A skin lesion imaged with a dermatoscope.
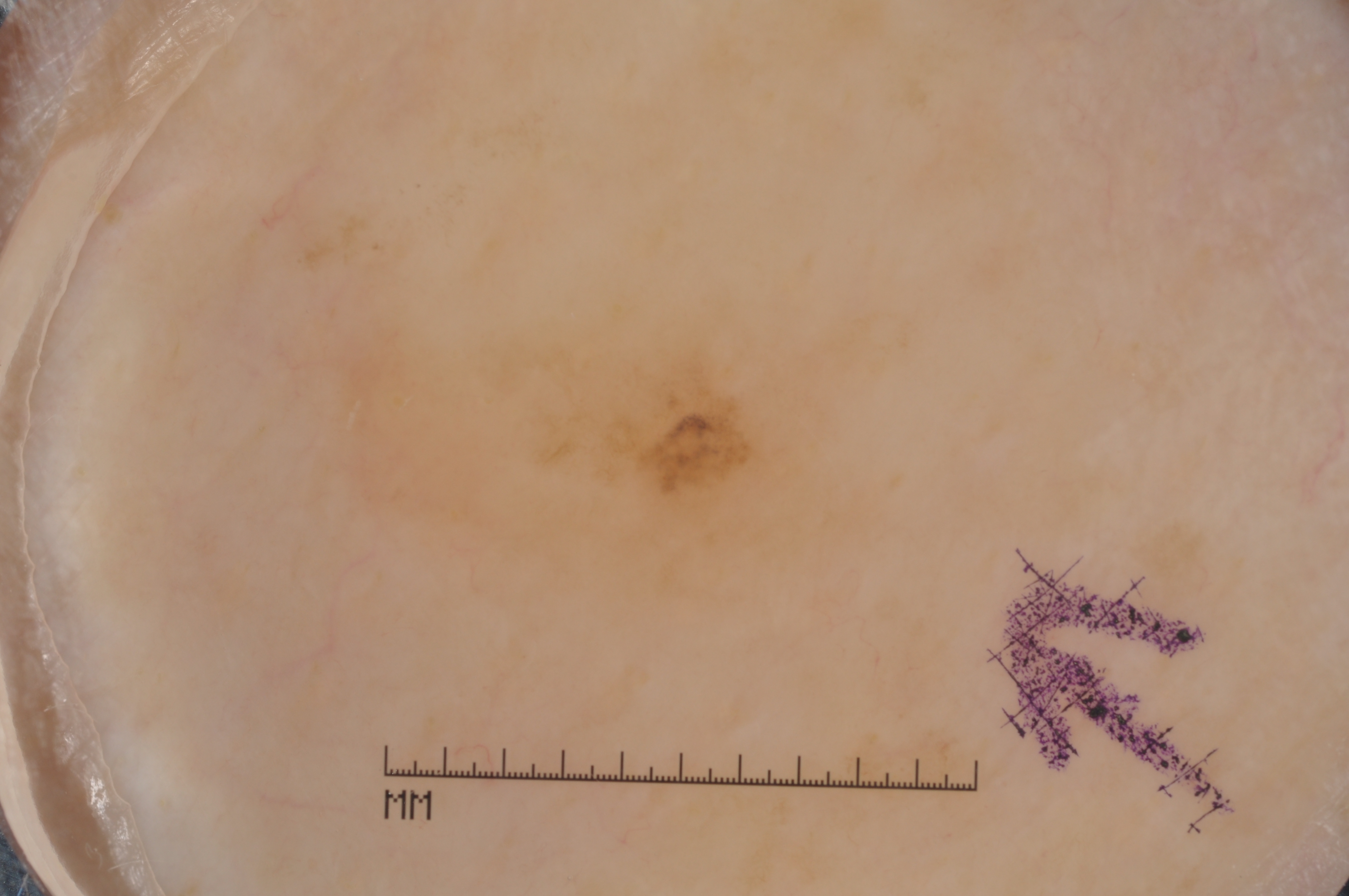dermoscopic features assessed but absent = pigment network, negative network, milia-like cysts, and streaks; bounding box = box(295, 309, 832, 595); size = ~10% of the field; diagnosis = a melanoma, a skin cancer.